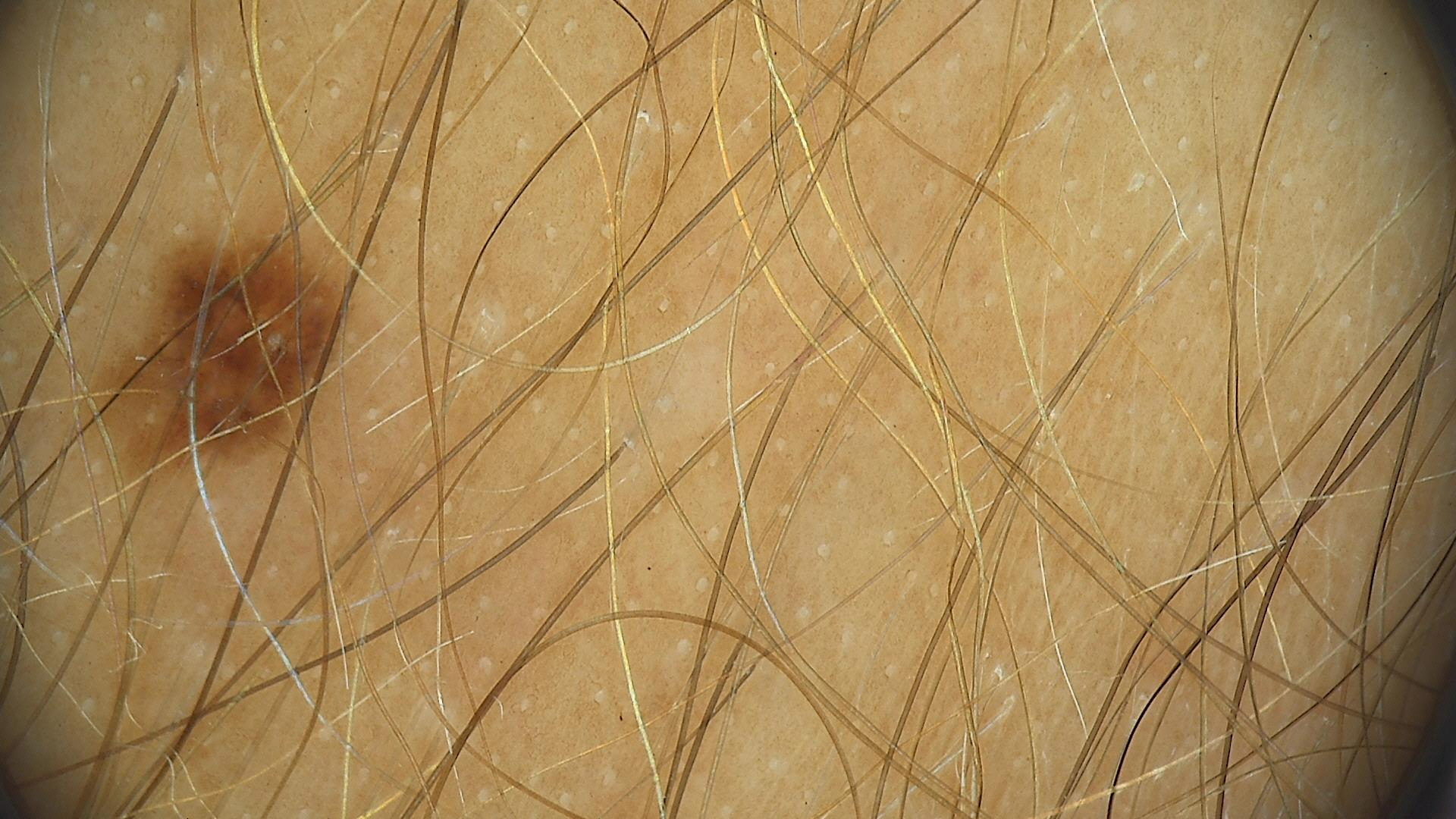diagnosis = dysplastic junctional nevus (expert consensus).